The photograph is a close-up of the affected area.
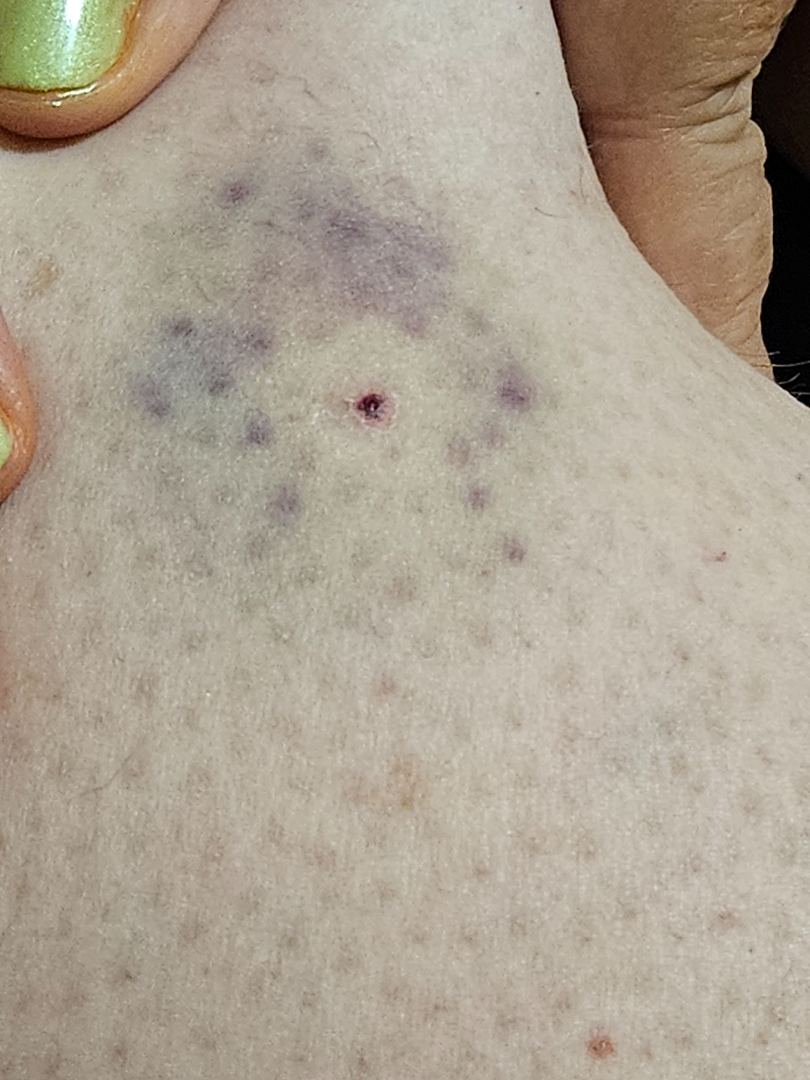On teledermatology review, Hemangioma, Insect Bite and Pyogenic granuloma were considered with similar weight.